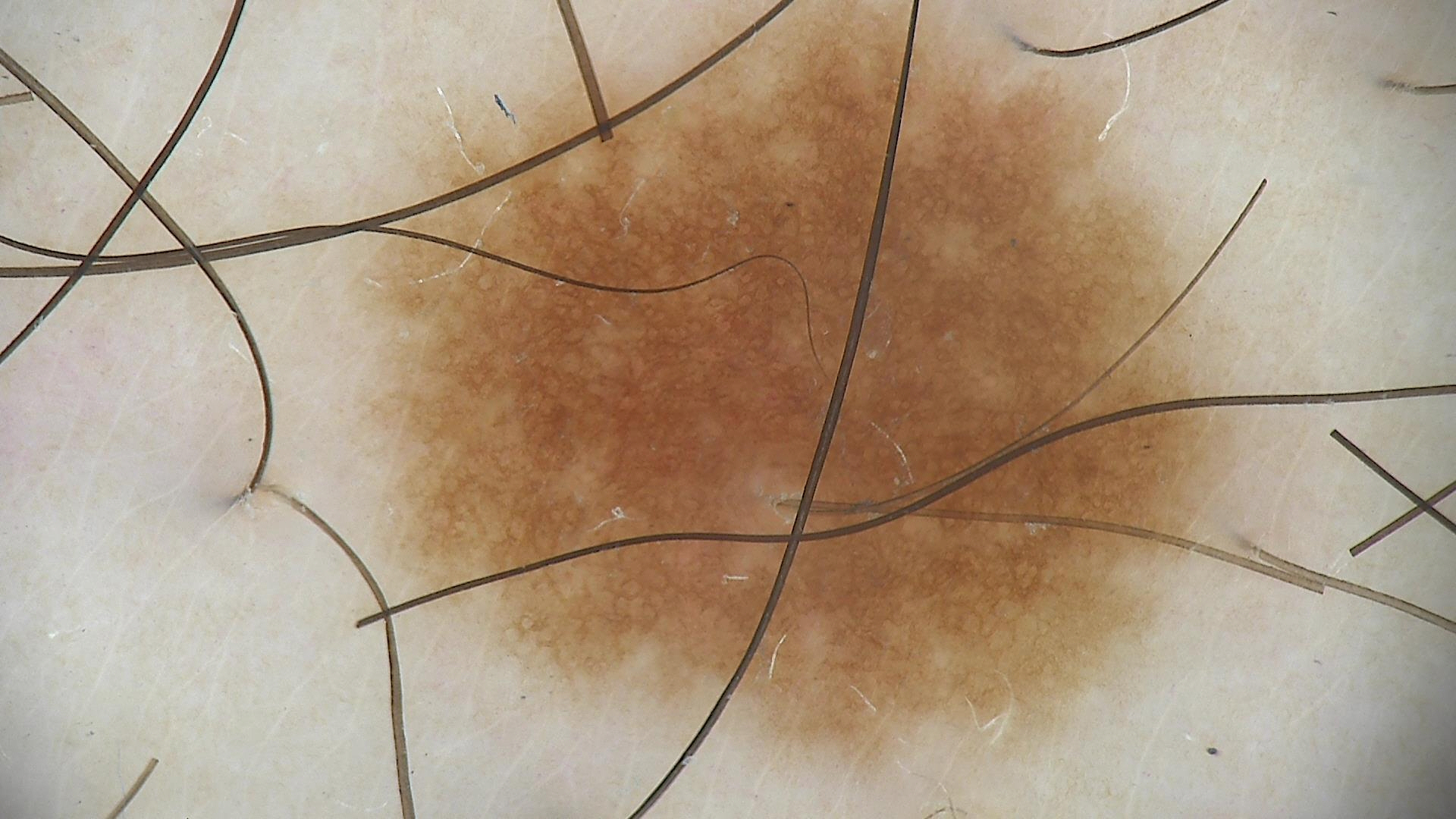A skin lesion imaged with a dermatoscope. Consistent with a dysplastic junctional nevus.